Imaged for a research study, with no referral diagnosis recorded; a female patient 48 years of age; a skin lesion imaged with a dermatoscope.
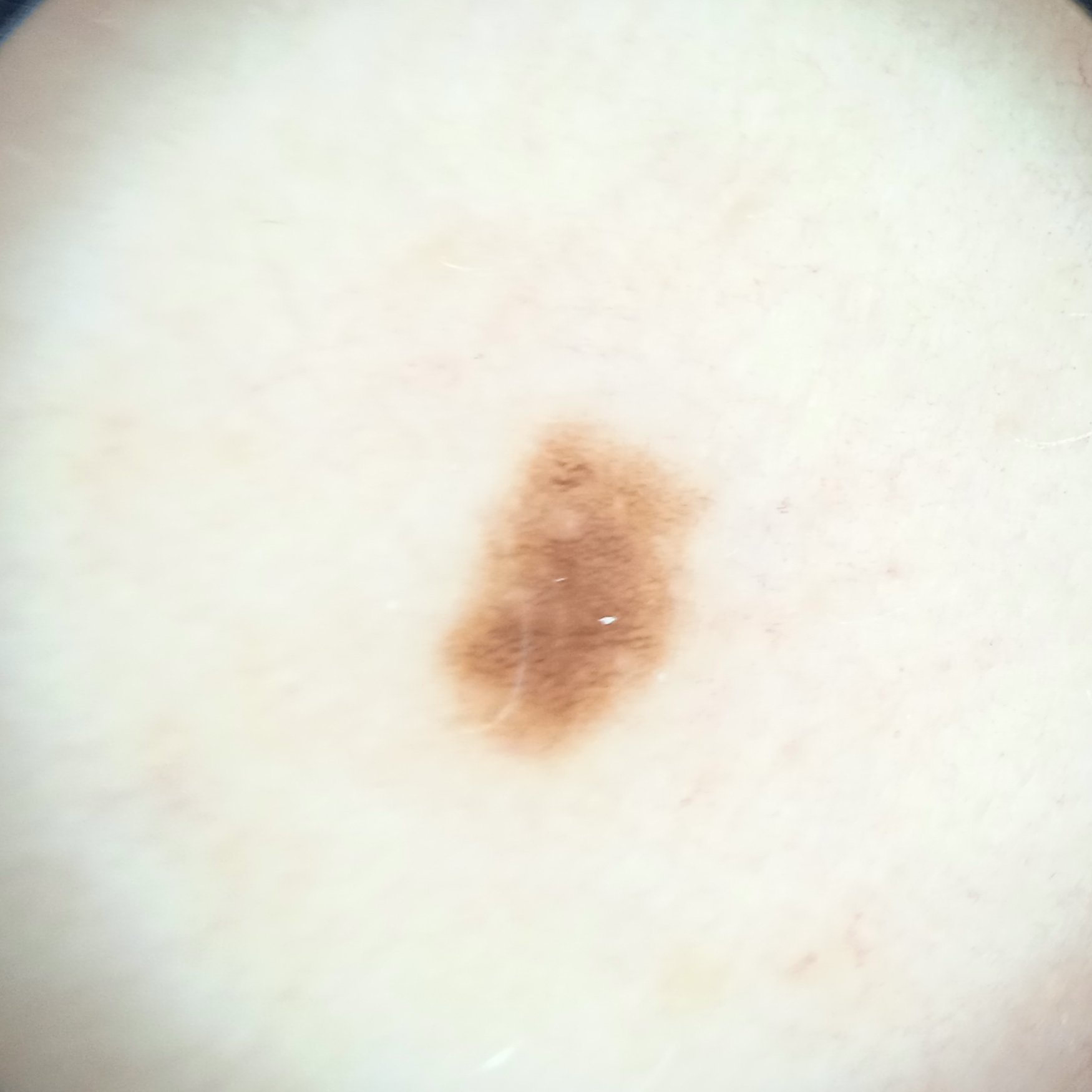Case summary:
Located on the torso. The lesion is about 4.3 mm across.
Conclusion:
The dermatologists' assessment was a melanocytic nevus.